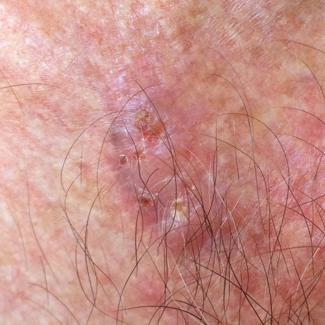Case summary: The patient was assessed as FST II. A male subject 47 years of age. A clinical close-up photograph of a skin lesion. The lesion is on the chest. Per patient report, the lesion is elevated, has grown, itches, and has bled. Diagnosis: Biopsy-confirmed as a basal cell carcinoma.